The affected area is the back of the torso; associated systemic symptoms include chills; texture is reported as fluid-filled, rough or flaky and raised or bumpy; skin tone: Fitzpatrick II; the patient is female; the photo was captured at an angle; the condition has been present for one to three months: 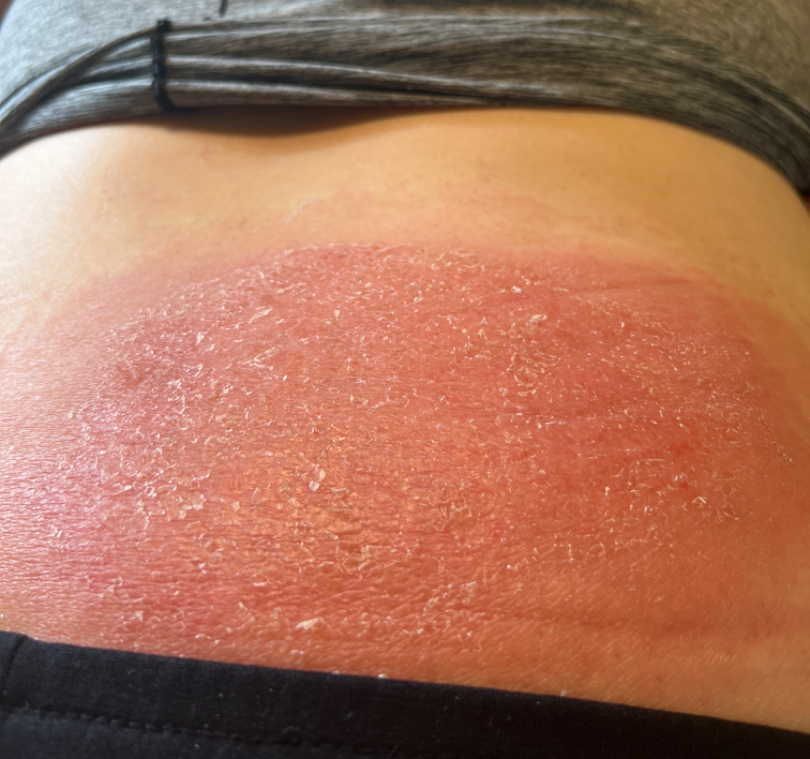differential:
  leading:
    - Cellulitis
  considered:
    - Allergic Contact Dermatitis
    - Erythema migrans